A macroscopic clinical photograph of a skin lesion; a female patient aged 73; the patient describes having few moles overall; acquired for a research image collection, with no referral diagnosis: 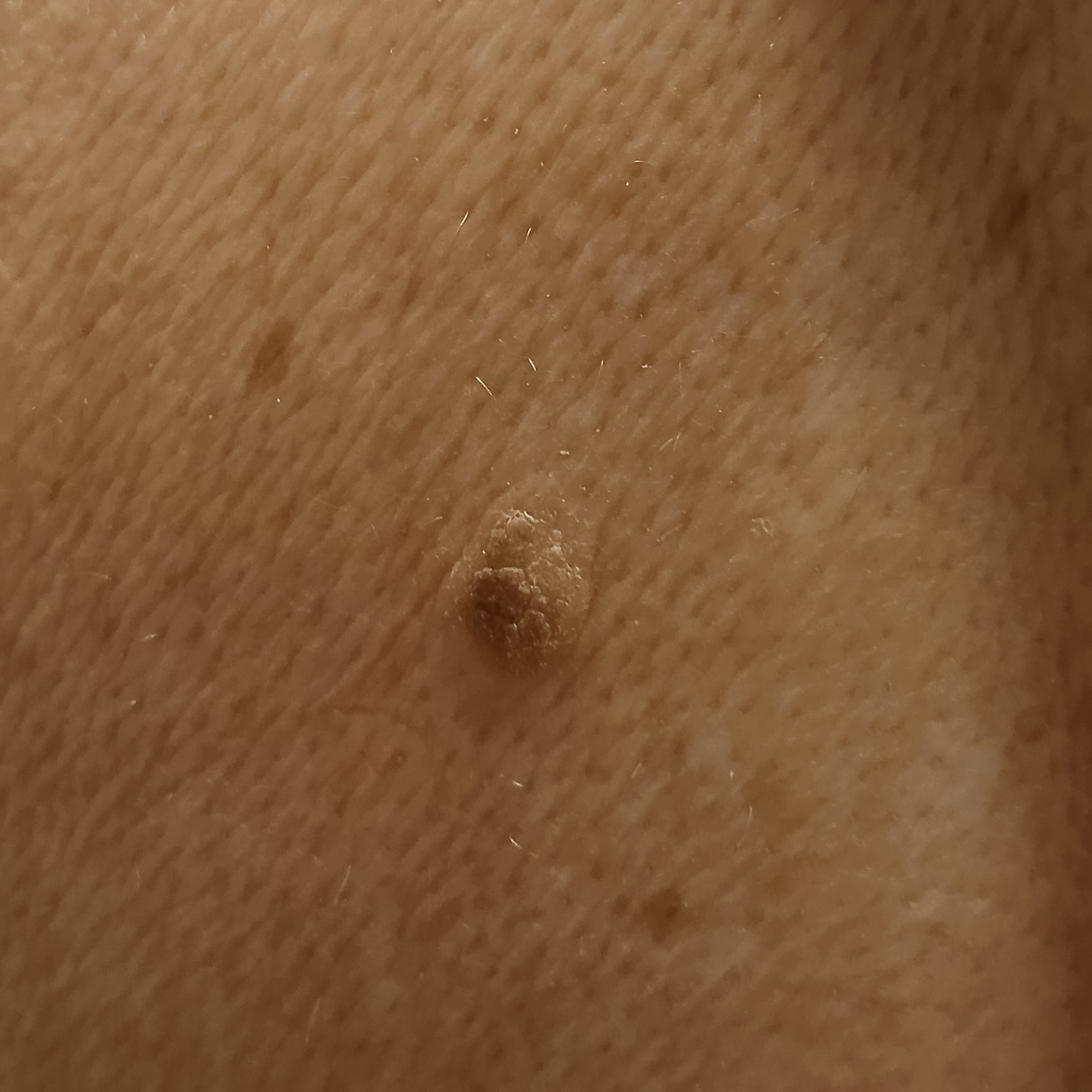Located on the back. The lesion is about 8.6 mm across. The dermatologists' assessment was a seborrheic keratosis.